The condition has been present for one to four weeks. Reported lesion symptoms include bothersome appearance. The sole of the foot is involved. Close-up view. The patient reports the lesion is rough or flaky — 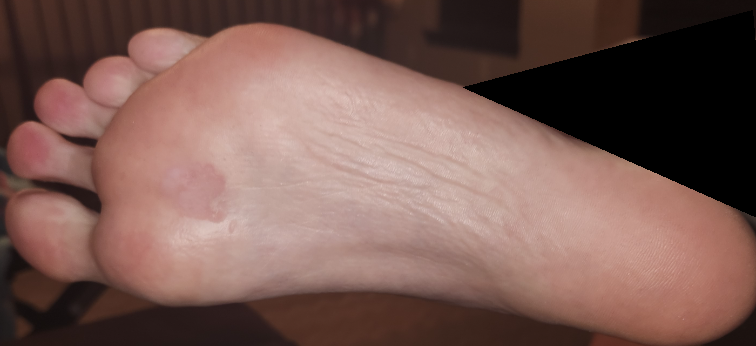The skin condition could not be confidently assessed from this image.